A smartphone photograph of a skin lesion:
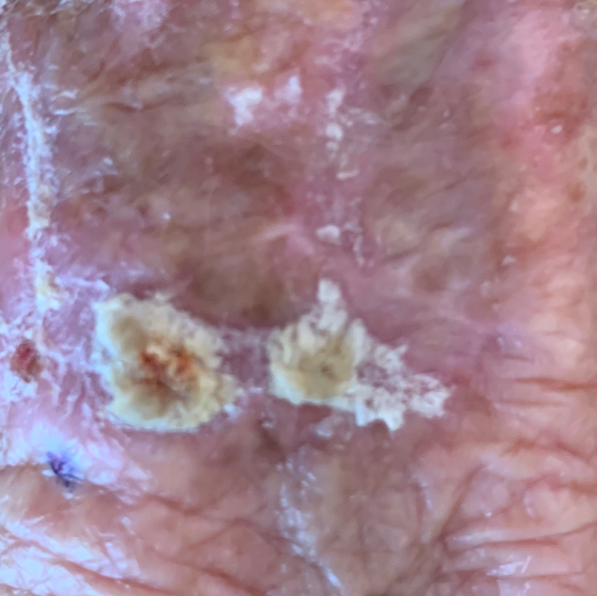Case summary:
The lesion involves a hand. The lesion measures 26 × 10 mm. The patient reports that the lesion is elevated.
Pathology:
On biopsy, the diagnosis was a malignancy — a basal cell carcinoma.